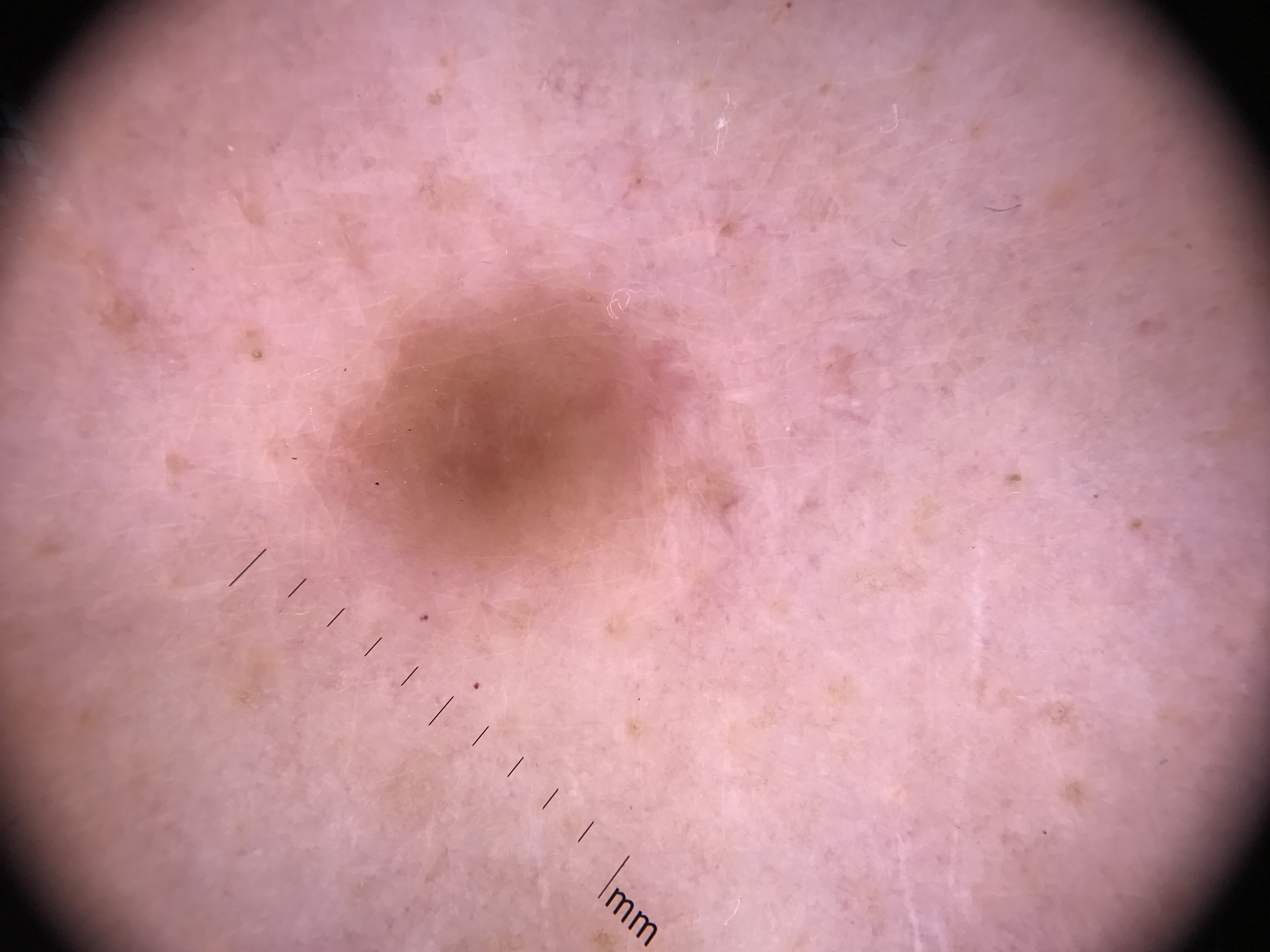A dermoscopic photograph of a skin lesion. Labeled as a dysplastic junctional nevus.